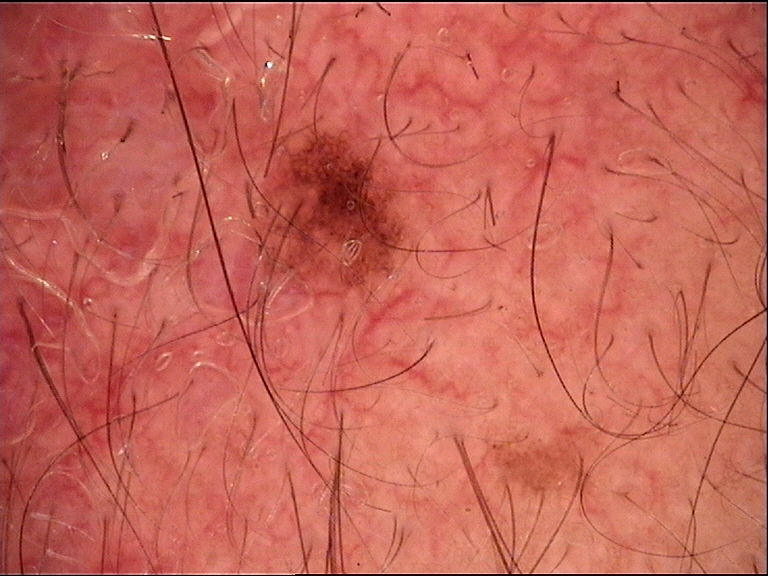* imaging: dermoscopy
* assessment: junctional nevus (expert consensus)